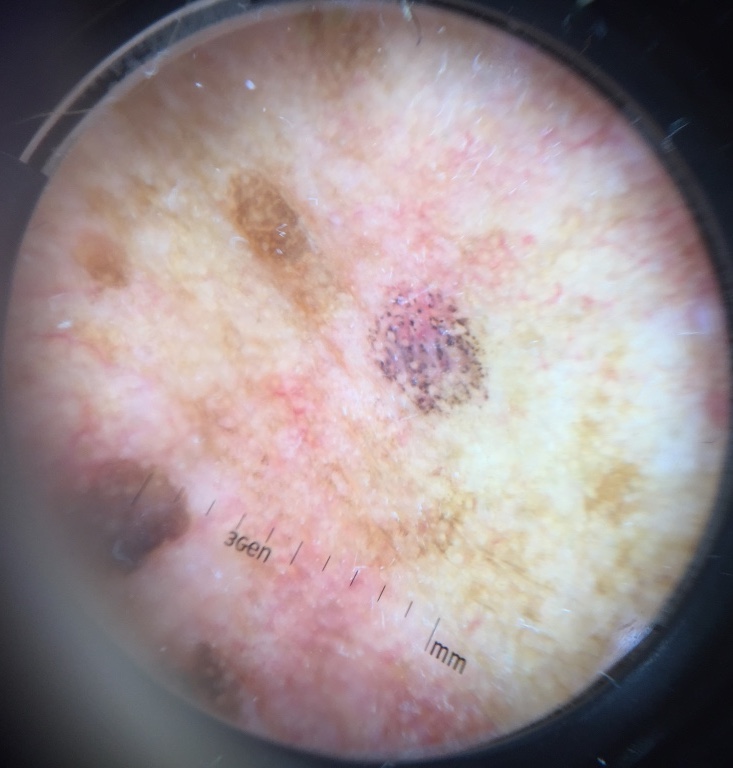<lesion>
  <diagnosis>
    <name>basal cell carcinoma</name>
    <code>bcc</code>
    <malignancy>malignant</malignancy>
    <super_class>non-melanocytic</super_class>
    <confirmation>histopathology</confirmation>
  </diagnosis>
</lesion>